A clinical photo of a skin lesion taken with a smartphone · a patient 54 years old: 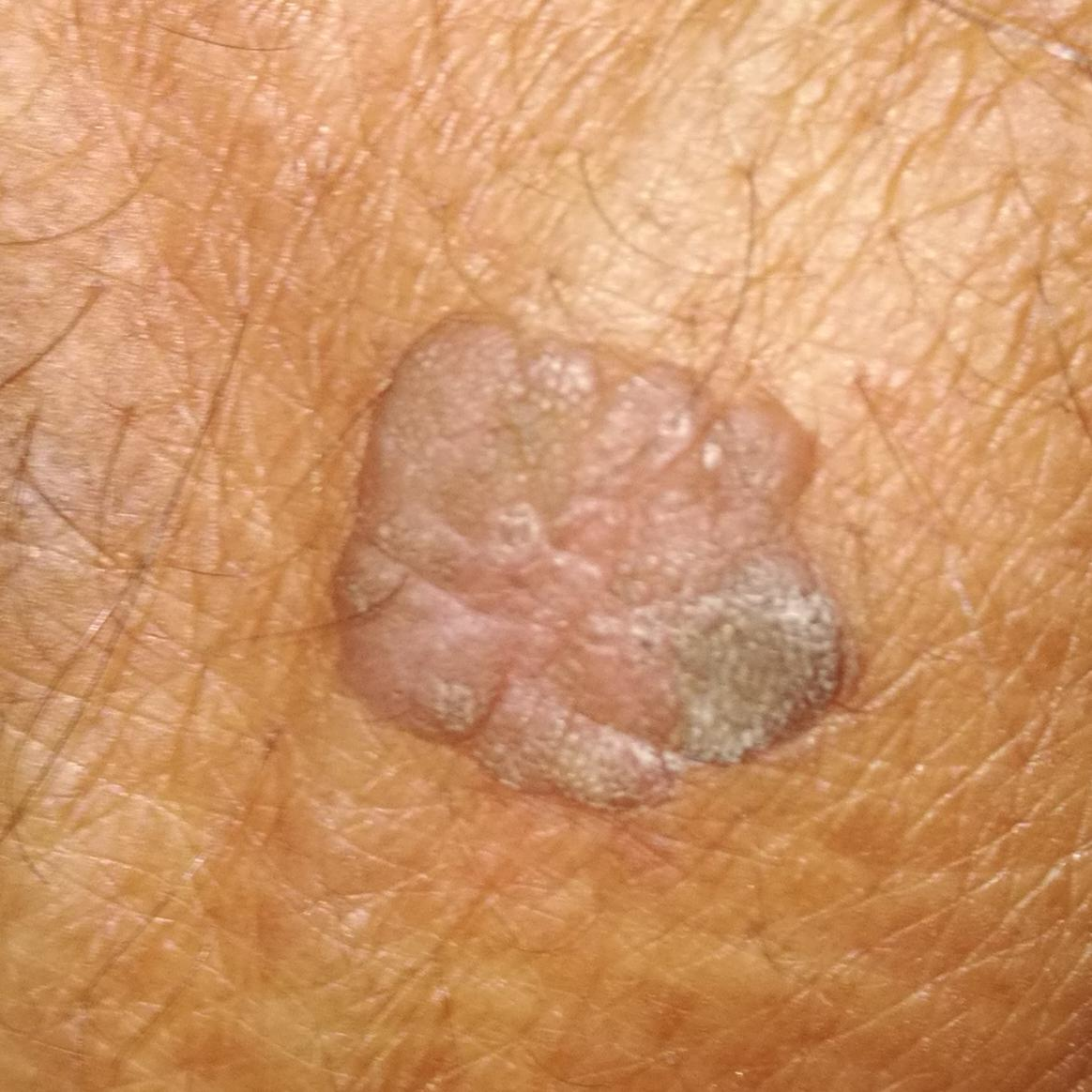site: an arm
symptoms: itching, elevation, growth / no change in appearance, no bleeding
diagnostic label: seborrheic keratosis (clinical consensus)